A smartphone photograph of a skin lesion. A female patient 77 years of age: 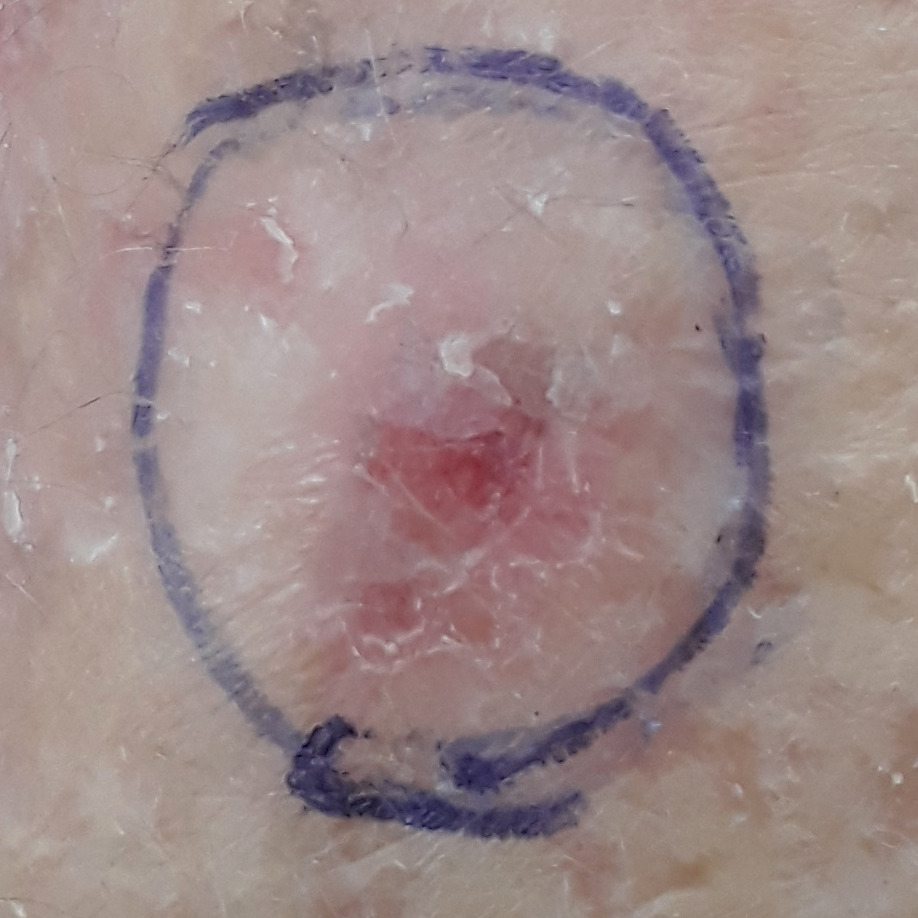Case:
• body site · a forearm
• reported symptoms · bleeding, itching, growth, elevation
• pathology · actinic keratosis (biopsy-proven)